A dermatoscopic image of a skin lesion: 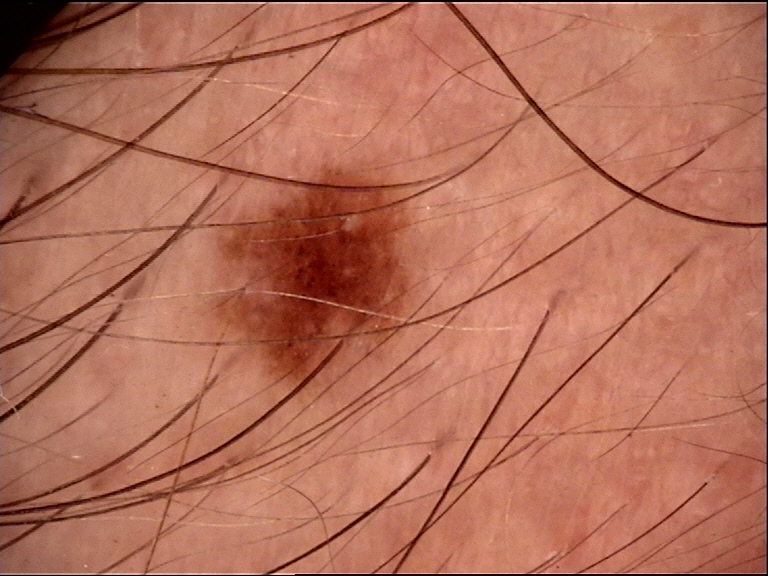Diagnosed as a dysplastic junctional nevus.